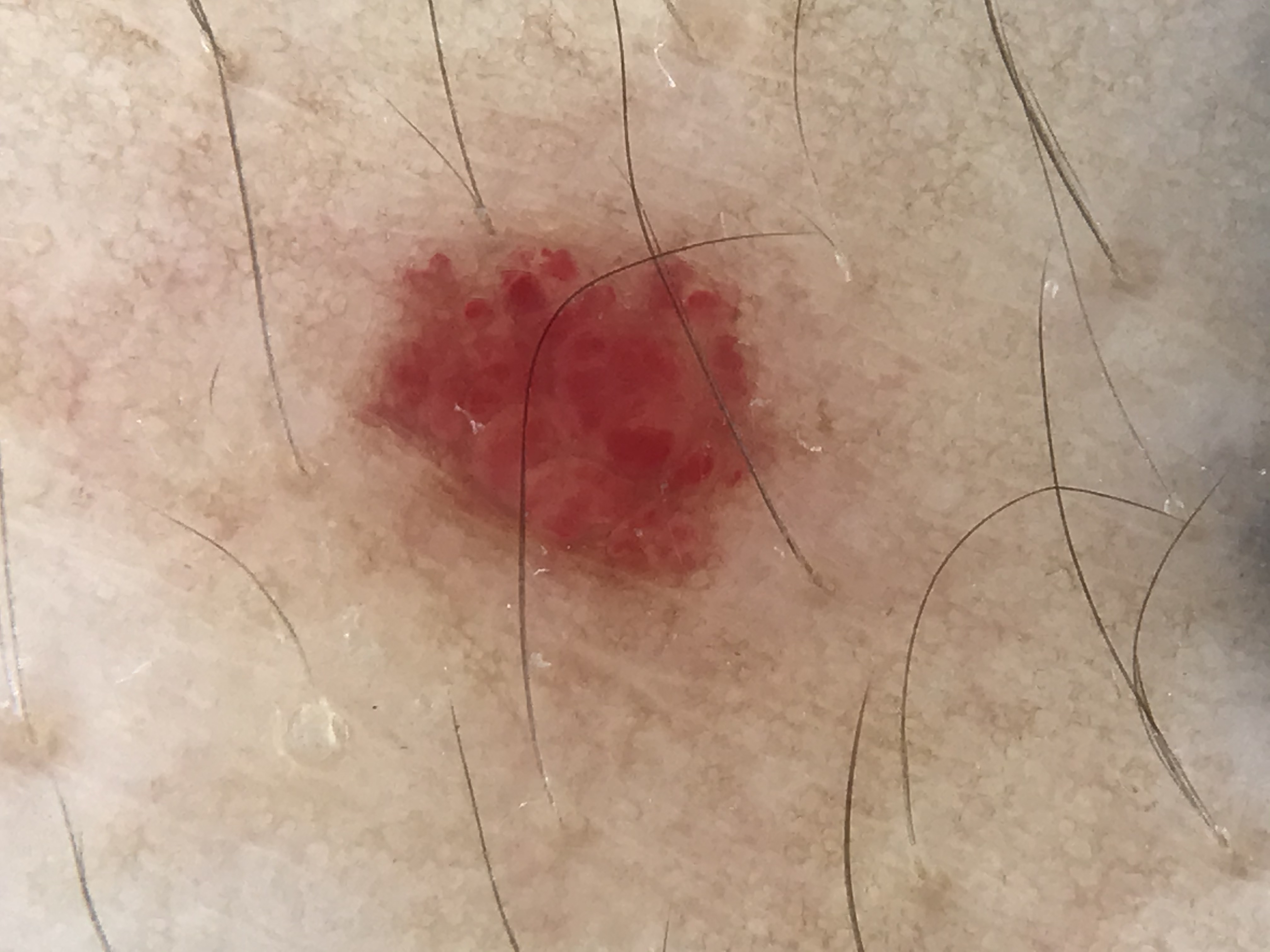Case: A dermoscopic close-up of a skin lesion. Conclusion: Classified as a hemangioma.